A dermoscopy image of a single skin lesion; the patient is a female aged around 45 — 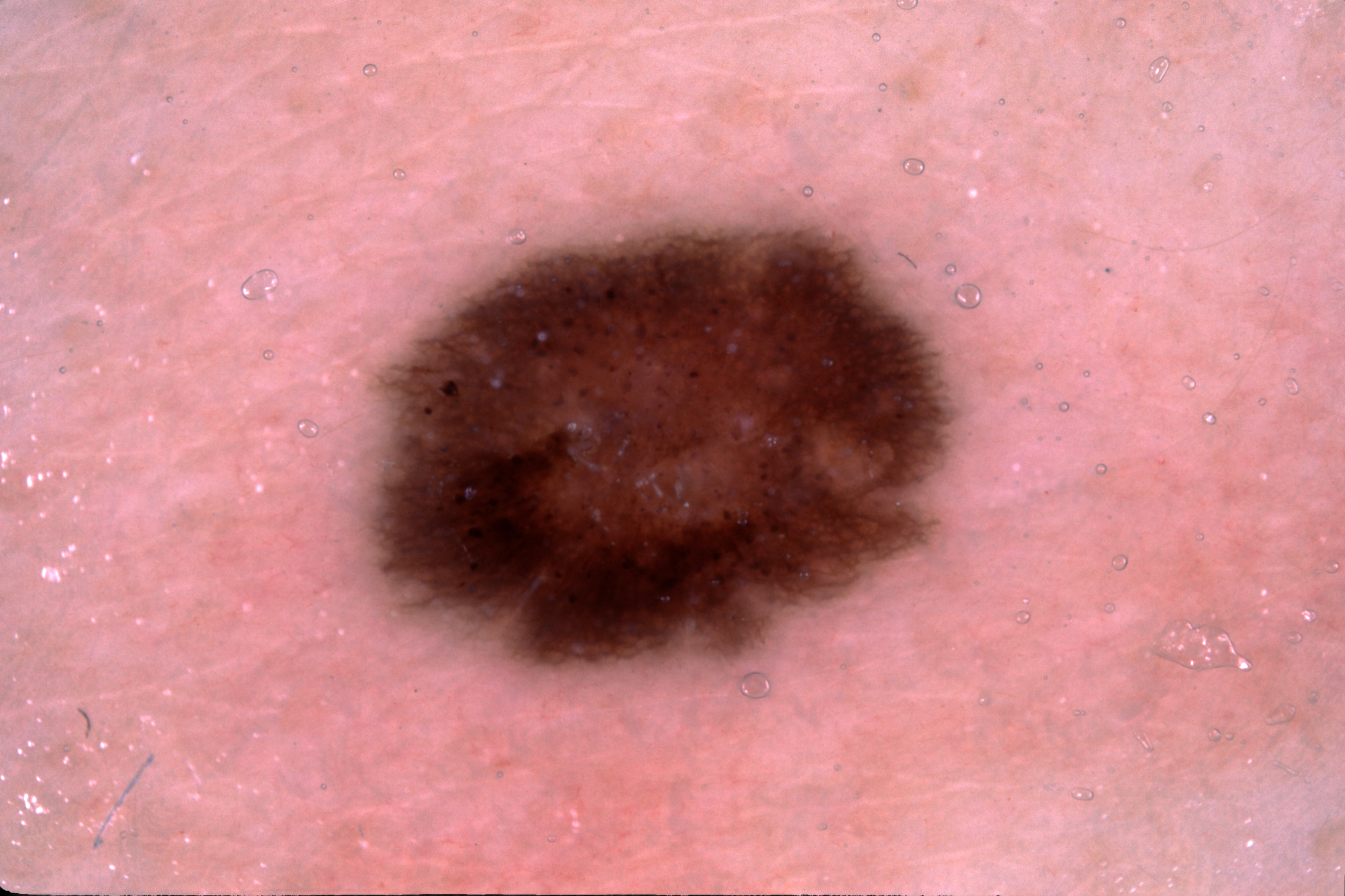Lesion location: x1=378, y1=231, x2=945, y2=672.
Dermoscopically, the lesion shows pigment network.
The lesion takes up a moderate portion of the field.
The diagnostic assessment was a melanocytic nevus.